A female patient approximately 15 years of age · a dermoscopic image of a skin lesion — 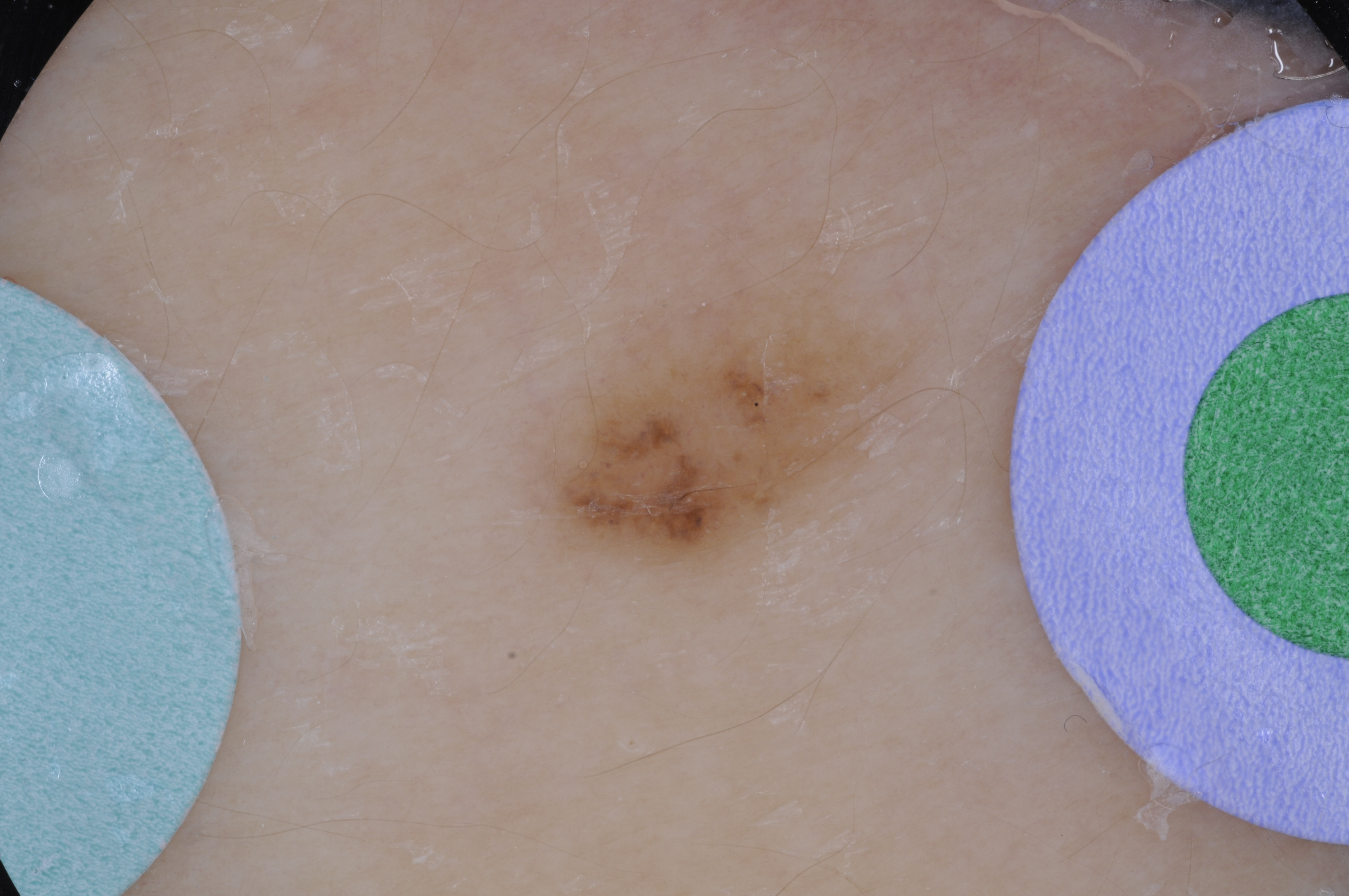| field | value |
|---|---|
| lesion size | ~7% of the field |
| dermoscopic features assessed but absent | milia-like cysts, streaks, globules, pigment network, and negative network |
| location | <box>518, 292, 943, 571</box> |
| assessment | a melanocytic nevus, a benign lesion |